A dermoscopic photograph of a skin lesion: 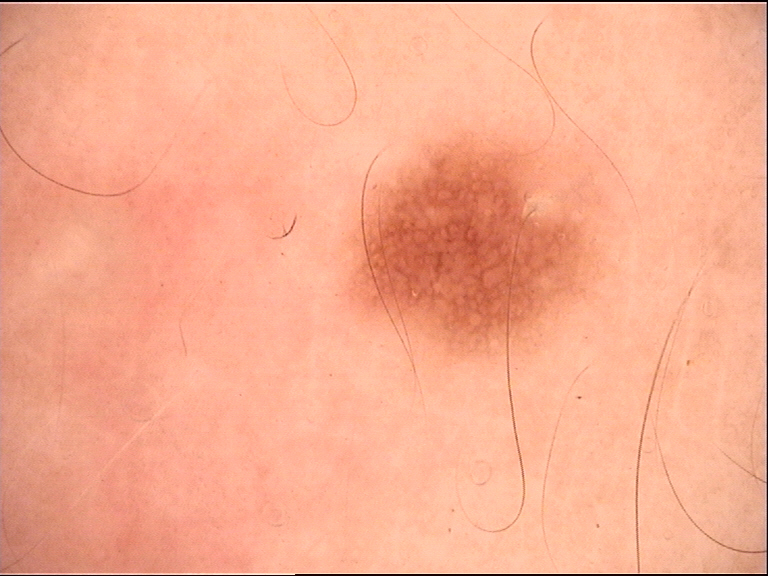This is a banal lesion. Diagnosed as a junctional nevus.